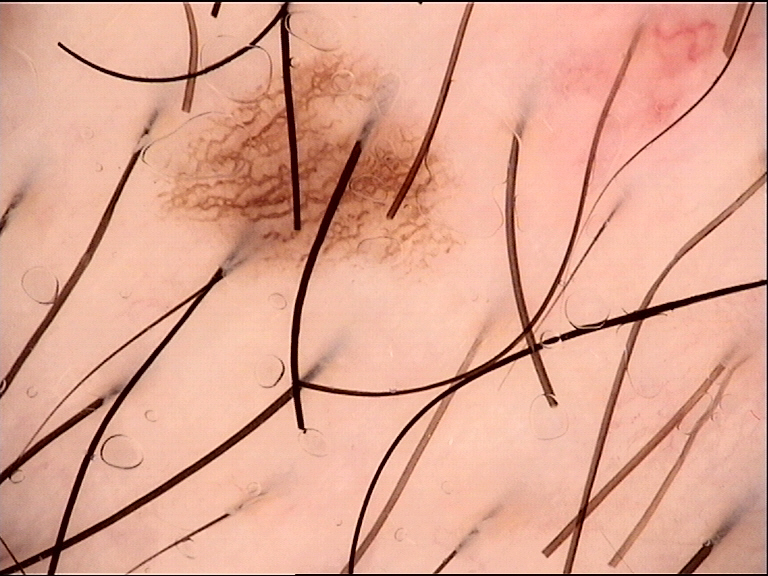Q: What was the diagnostic impression?
A: dysplastic junctional nevus (expert consensus)